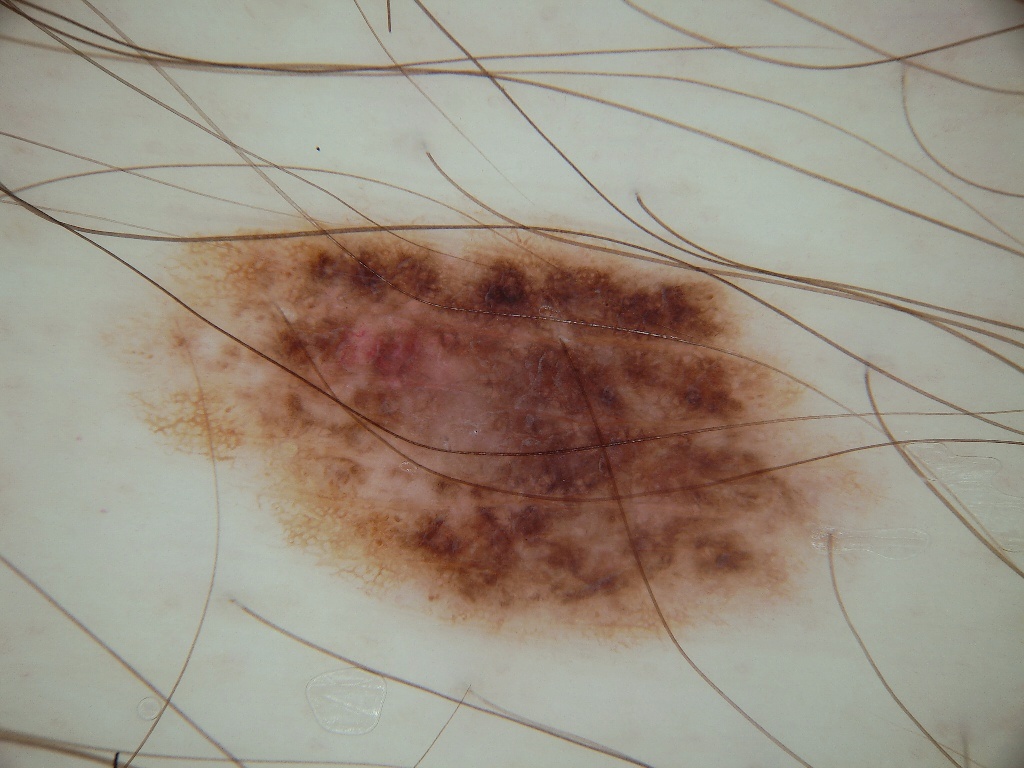- image type · dermoscopic image
- bounding box · 93 198 892 665
- diagnosis · a benign skin lesion